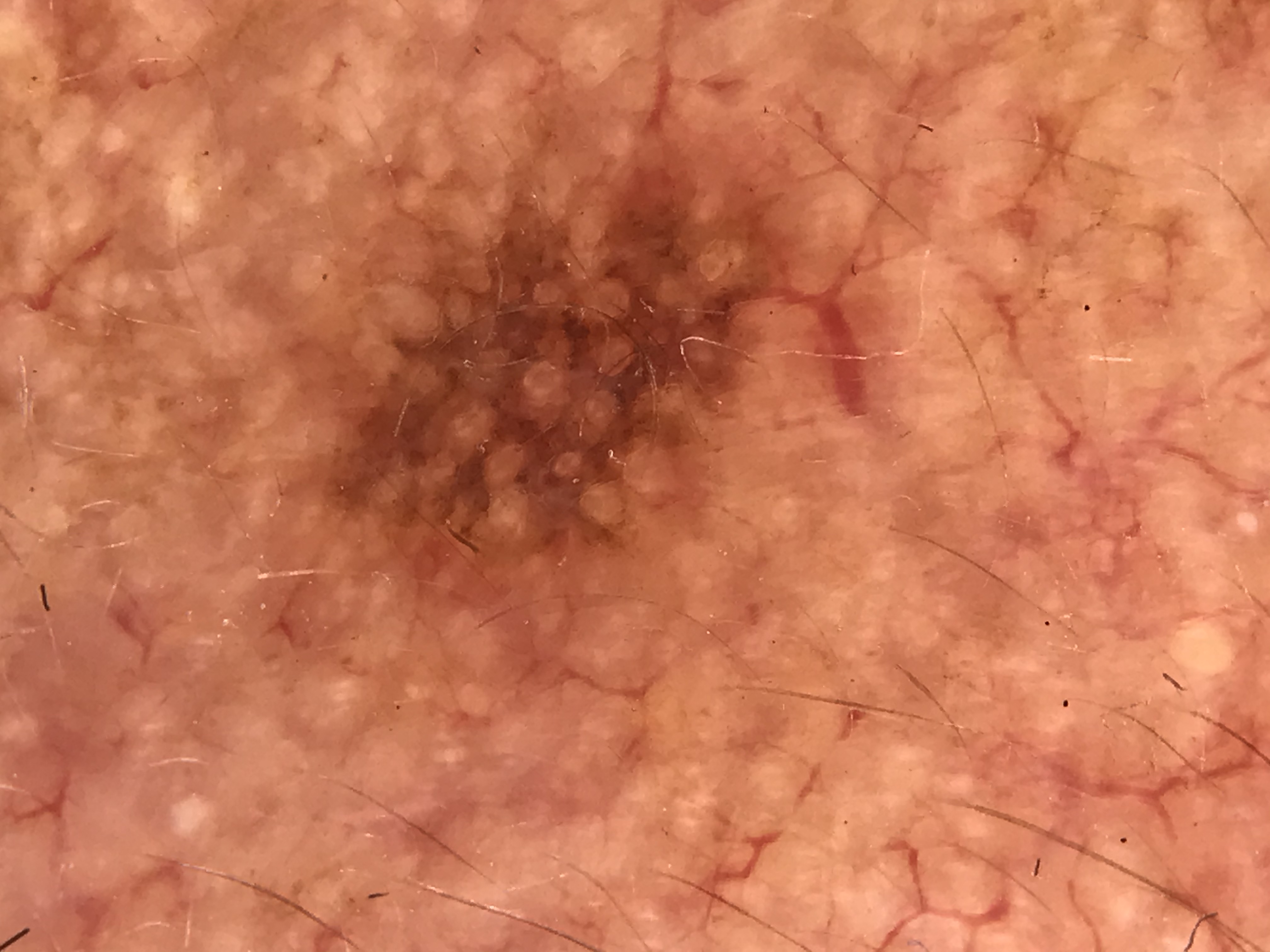A dermoscopic close-up of a skin lesion.
This is a keratinocytic lesion.
The diagnosis was an actinic keratosis.